A dermoscopic image of a skin lesion.
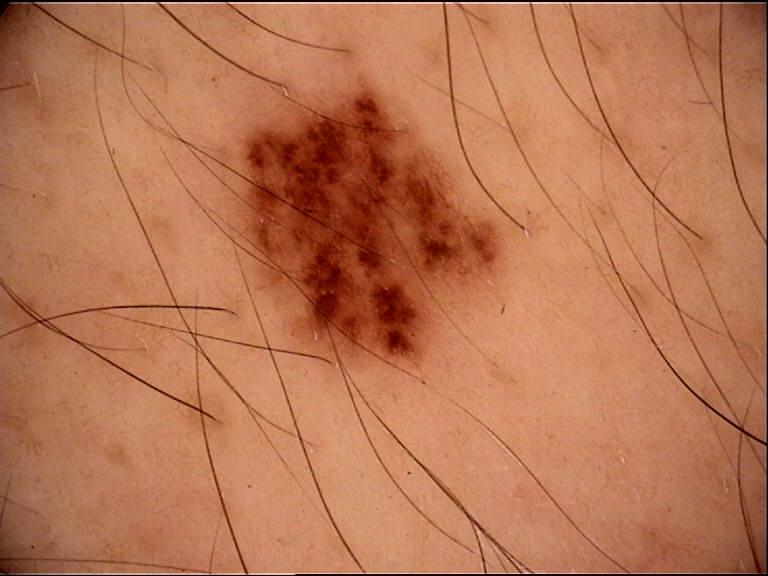Labeled as a benign lesion — a dysplastic junctional nevus.